This is a dermoscopic photograph of a skin lesion — 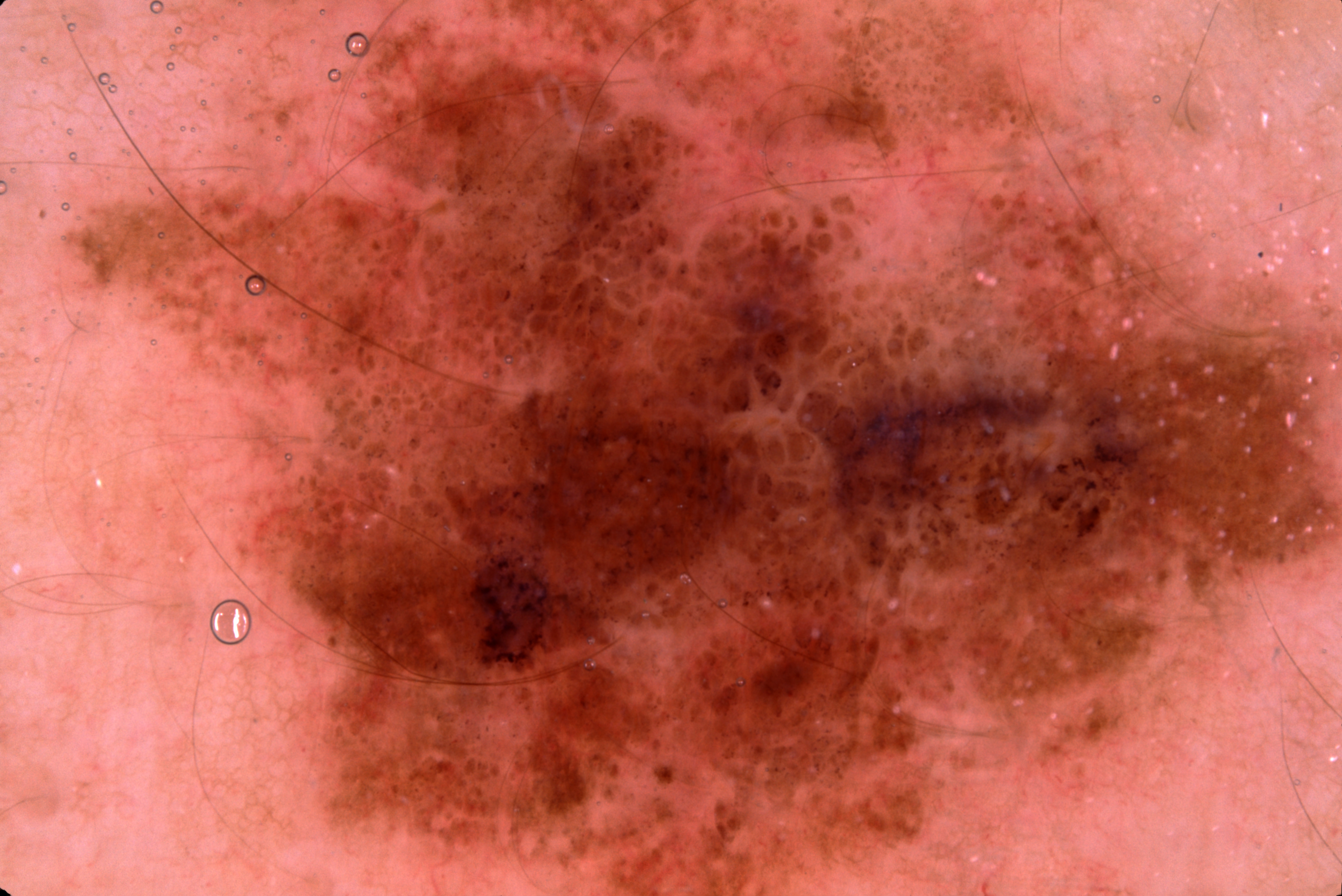On dermoscopy, the lesion shows milia-like cysts and negative network, with no pigment network or streaks. The lesion stretches across essentially the whole frame. The clinical diagnosis was a melanocytic nevus, a benign lesion.